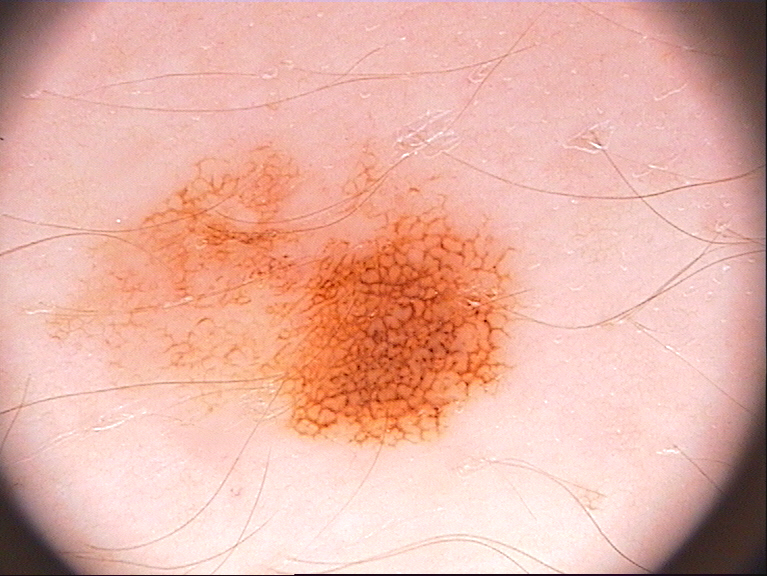A female patient approximately 40 years of age. A dermoscopic view of a skin lesion. The lesion takes up about 28% of the image. As (left, top, right, bottom), lesion location: 40, 123, 535, 455. Dermoscopic assessment notes globules and pigment network; no negative network, streaks, or milia-like cysts. The lesion was assessed as a melanocytic nevus.